The photograph was taken at an angle:
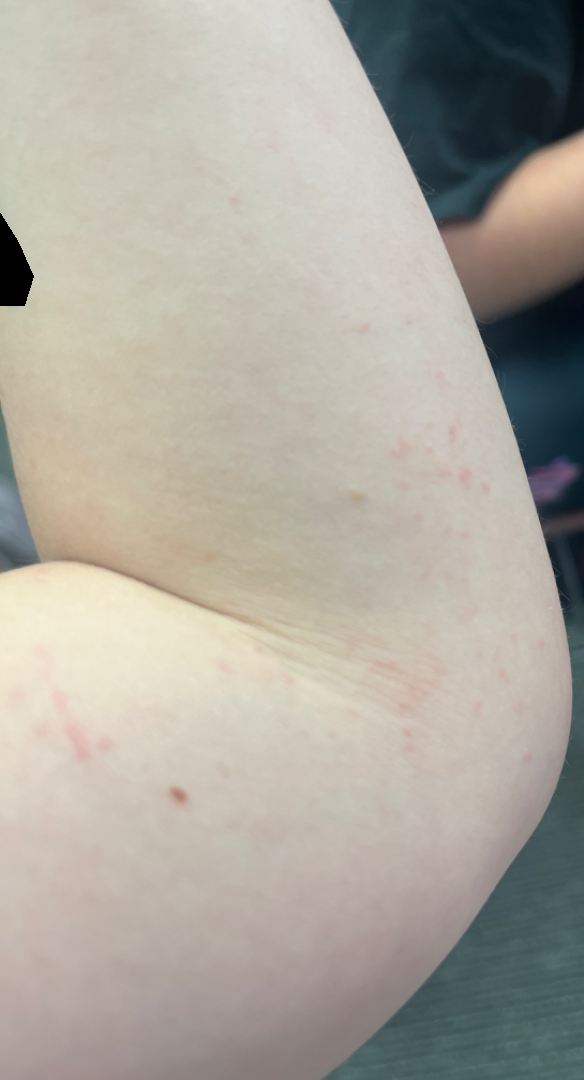Review: The reviewing dermatologist was unable to assign a differential diagnosis from the image.